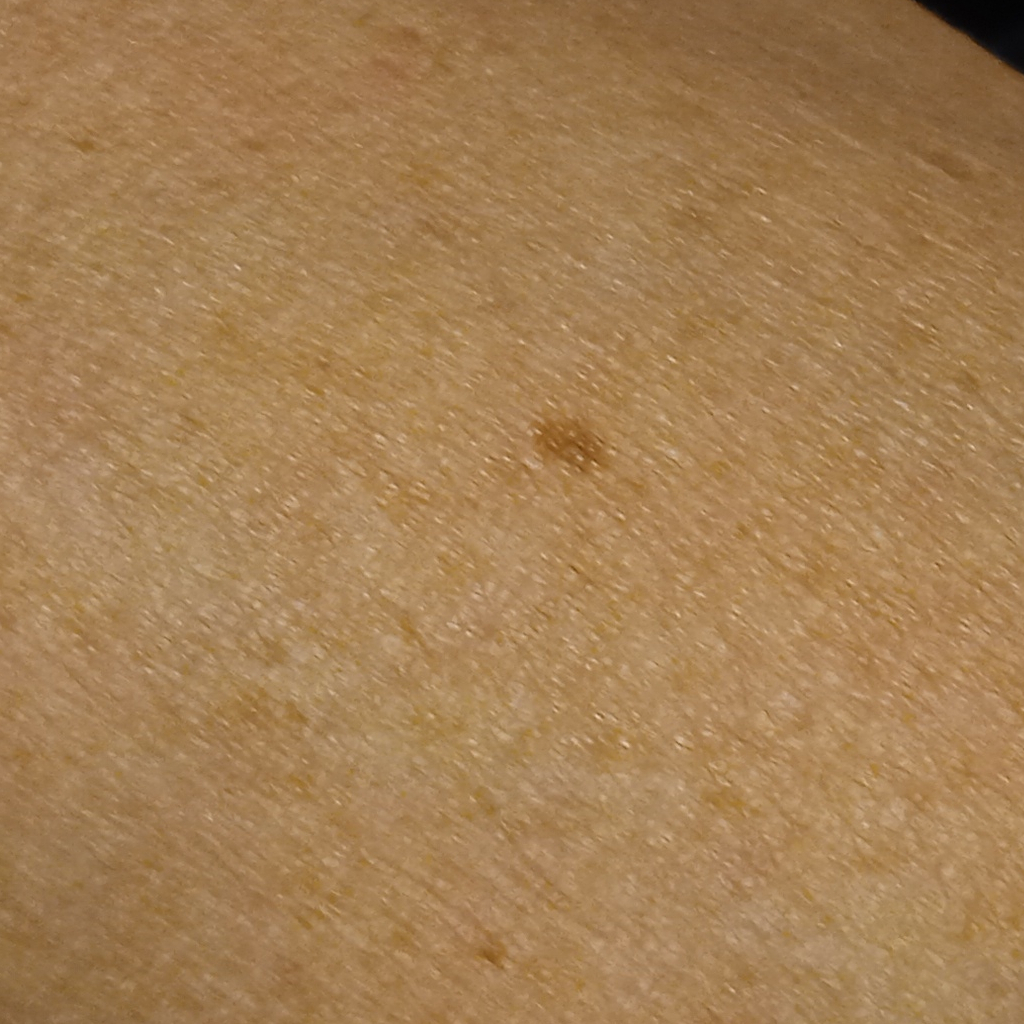Dermatologist review favored a melanocytic nevus.